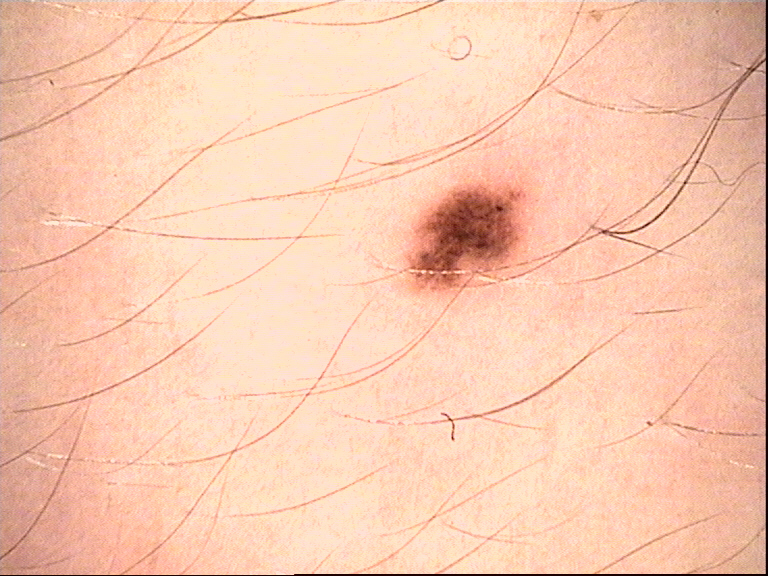Case:
A dermoscopic image of a skin lesion.
Conclusion:
Diagnosed as a dysplastic junctional nevus.